A dermoscopic close-up of a skin lesion:
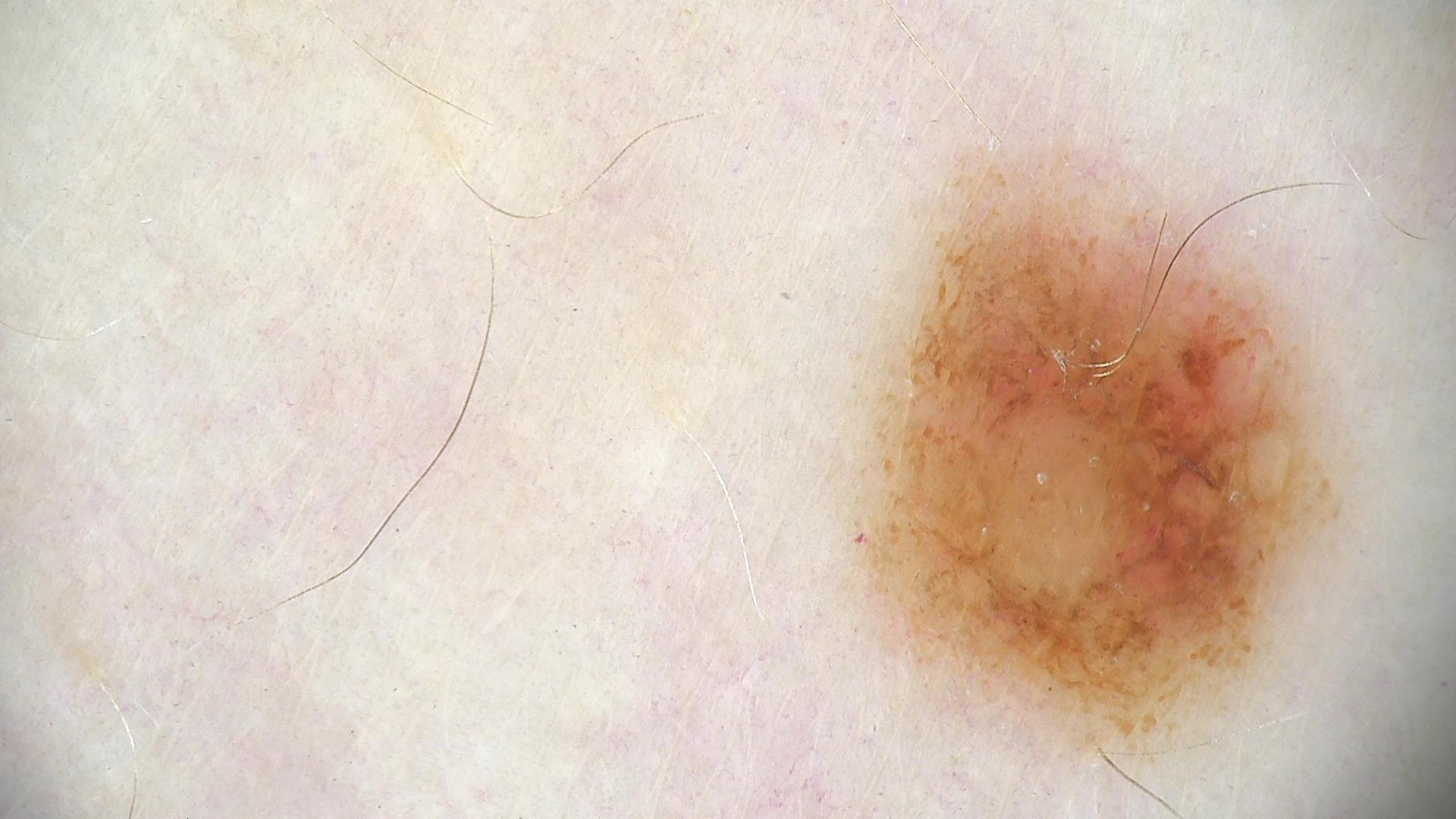The diagnosis was a banal lesion — a compound nevus.